The patient described the issue as a rash; present for less than one week; located on the back of the torso; the subject is a female aged 40–49; the patient indicates the lesion is fluid-filled and raised or bumpy; the photograph was taken at an angle; symptoms reported: burning, pain and itching: 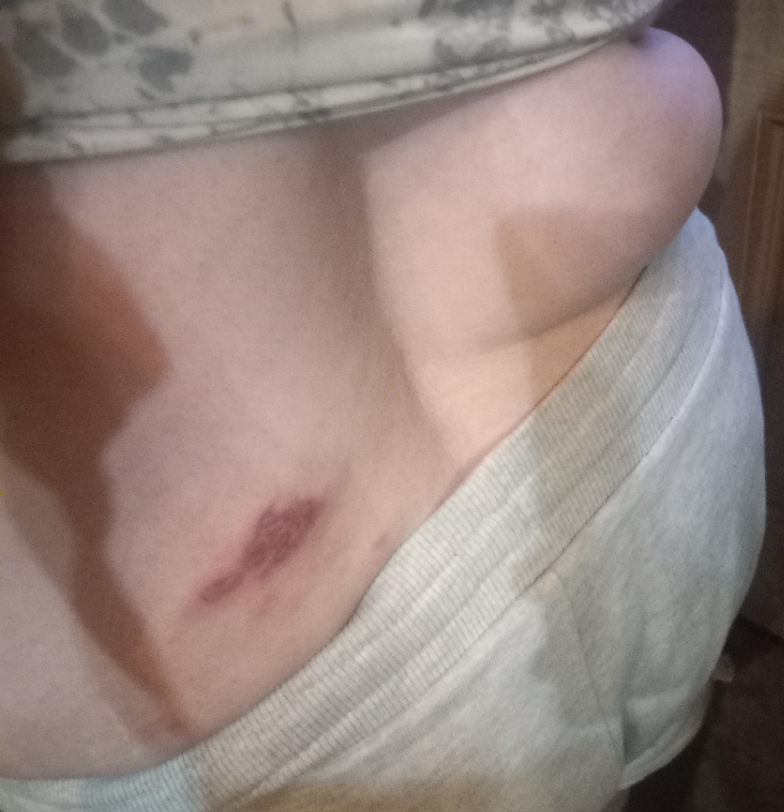{
  "differential": {
    "tied_lead": [
      "Herpes Zoster",
      "Herpes Simplex"
    ]
  }
}